A male patient 60 years of age · the patient says their skin reddens with sun exposure · the referring clinician suspected basal cell carcinoma: 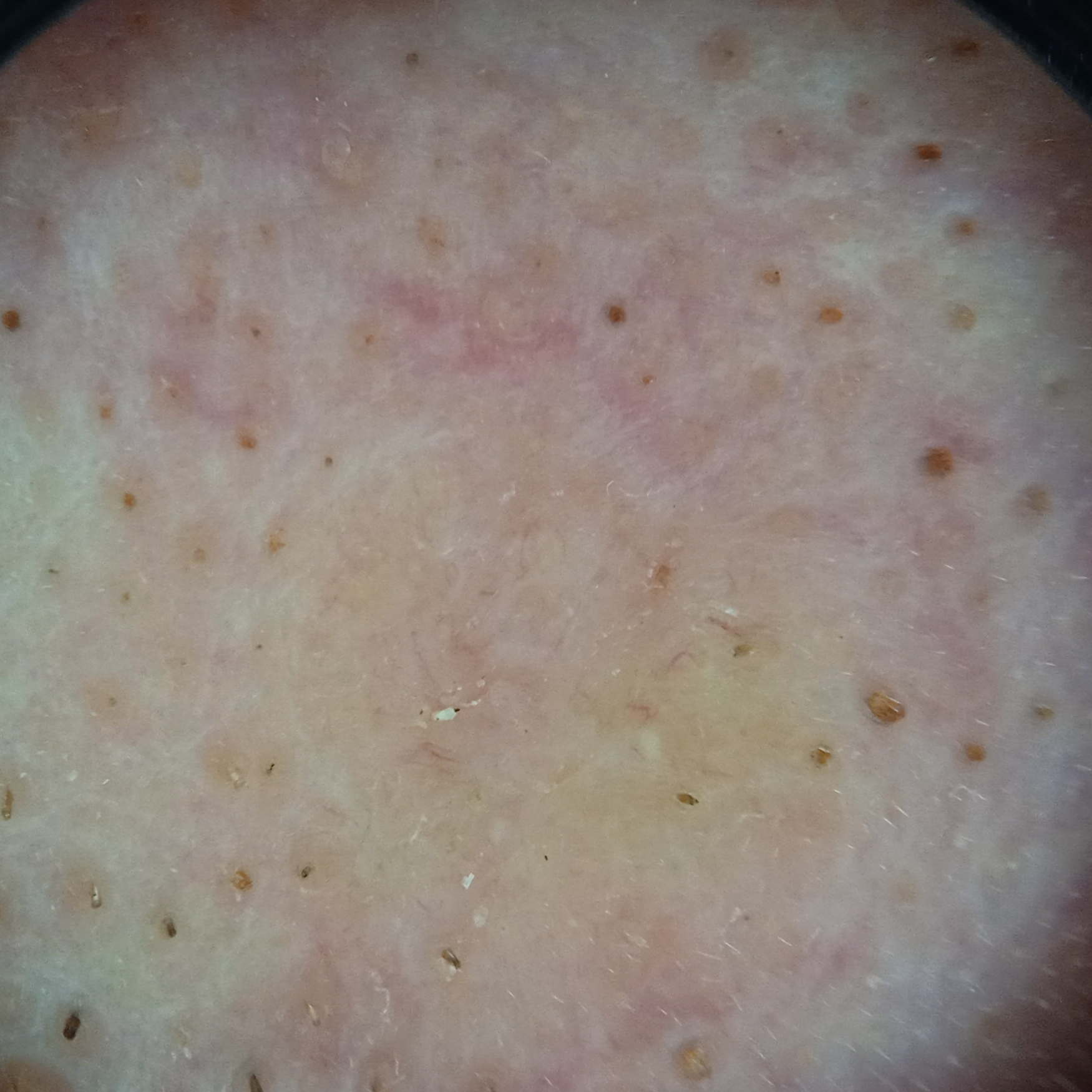Located on the face.
The lesion measures approximately 8.5 mm.
The biopsy diagnosis was a basal cell carcinoma, following excision, with a measured thickness of 1.7 mm.